The photograph is a close-up of the affected area, the head or neck is involved.
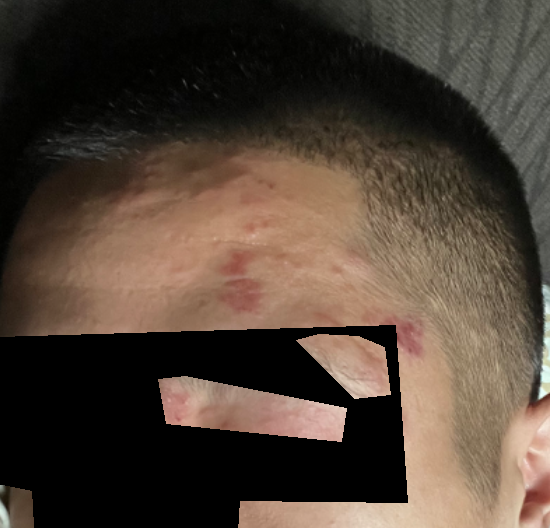<summary>
<assessment>indeterminate from the photograph</assessment>
<symptoms>pain, itching</symptoms>
<patient_category>acne</patient_category>
<texture>rough or flaky, raised or bumpy, fluid-filled</texture>
<duration>less than one week</duration>
</summary>